The chart notes a previous melanoma · a male patient in their mid- to late 60s — 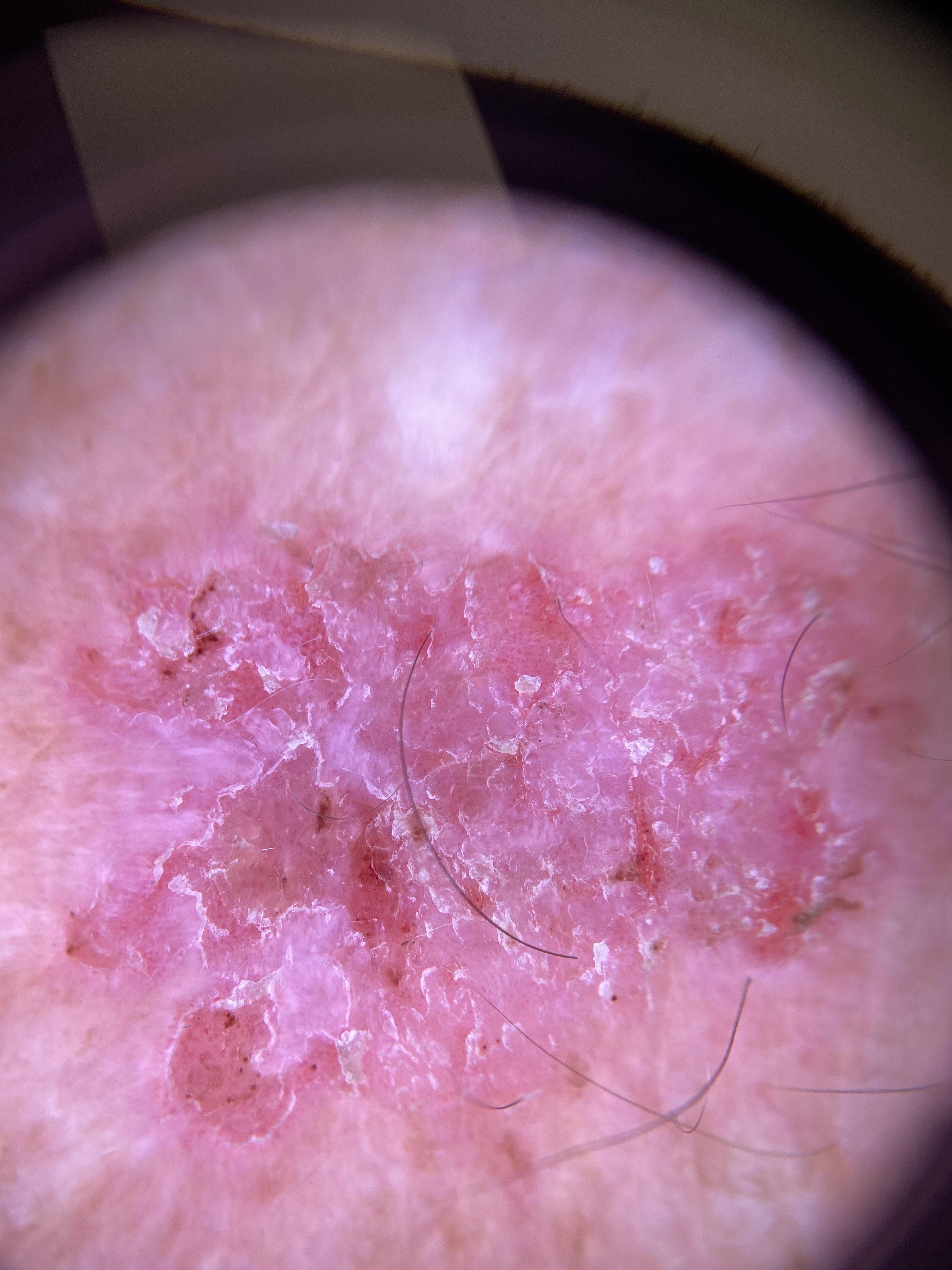diagnostic label: Squamous cell carcinoma (biopsy-proven)